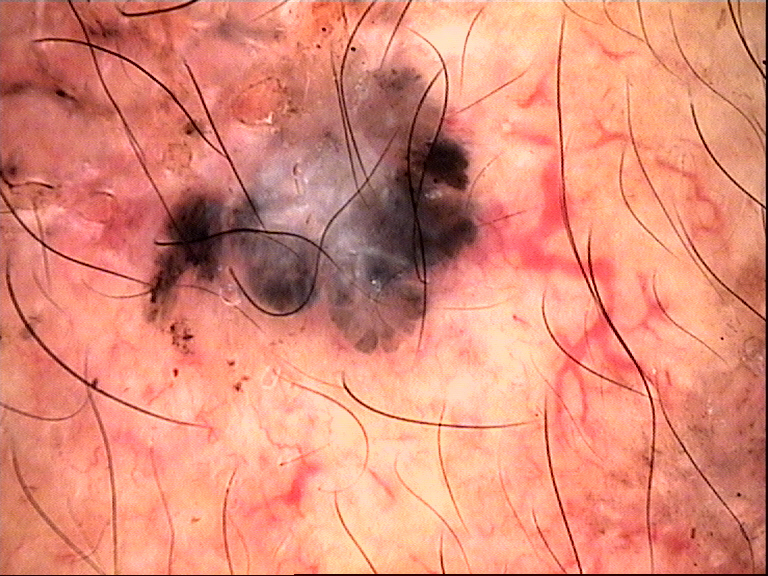A dermoscopic image of a skin lesion. Confirmed on histopathology as a basal cell carcinoma.